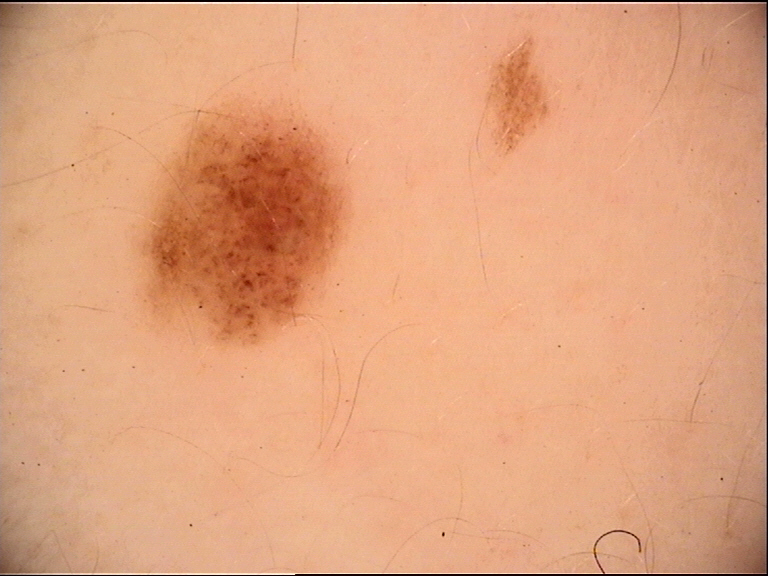image = dermatoscopy | diagnostic label = dysplastic junctional nevus (expert consensus).